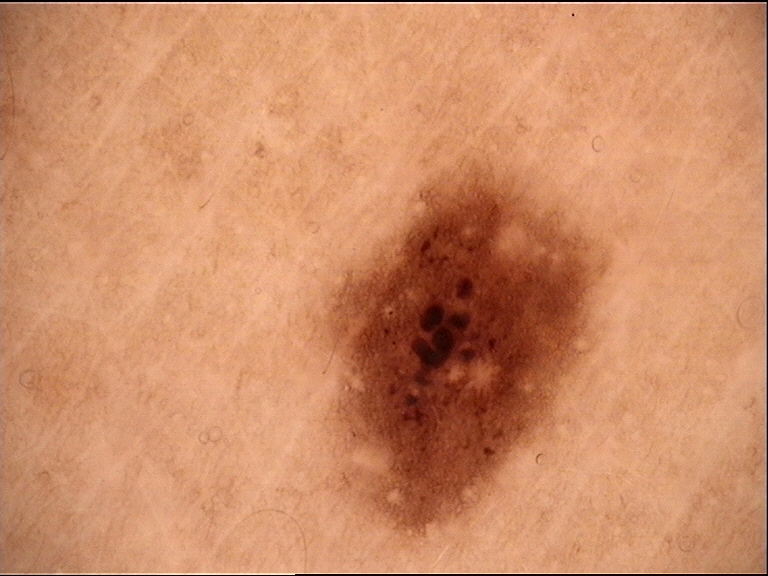imaging: dermoscopy | assessment: dysplastic junctional nevus (expert consensus).